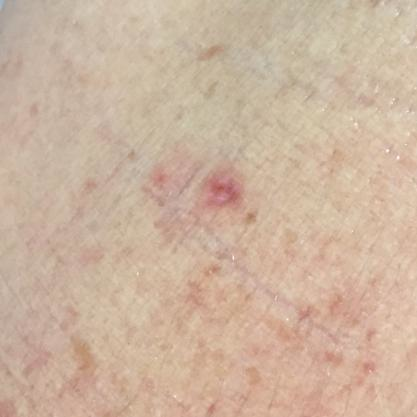A subject age 65.
A smartphone photograph of a skin lesion.
The lesion is on a forearm.
The patient describes that the lesion itches, but does not hurt.
The clinical impression was an actinic keratosis.